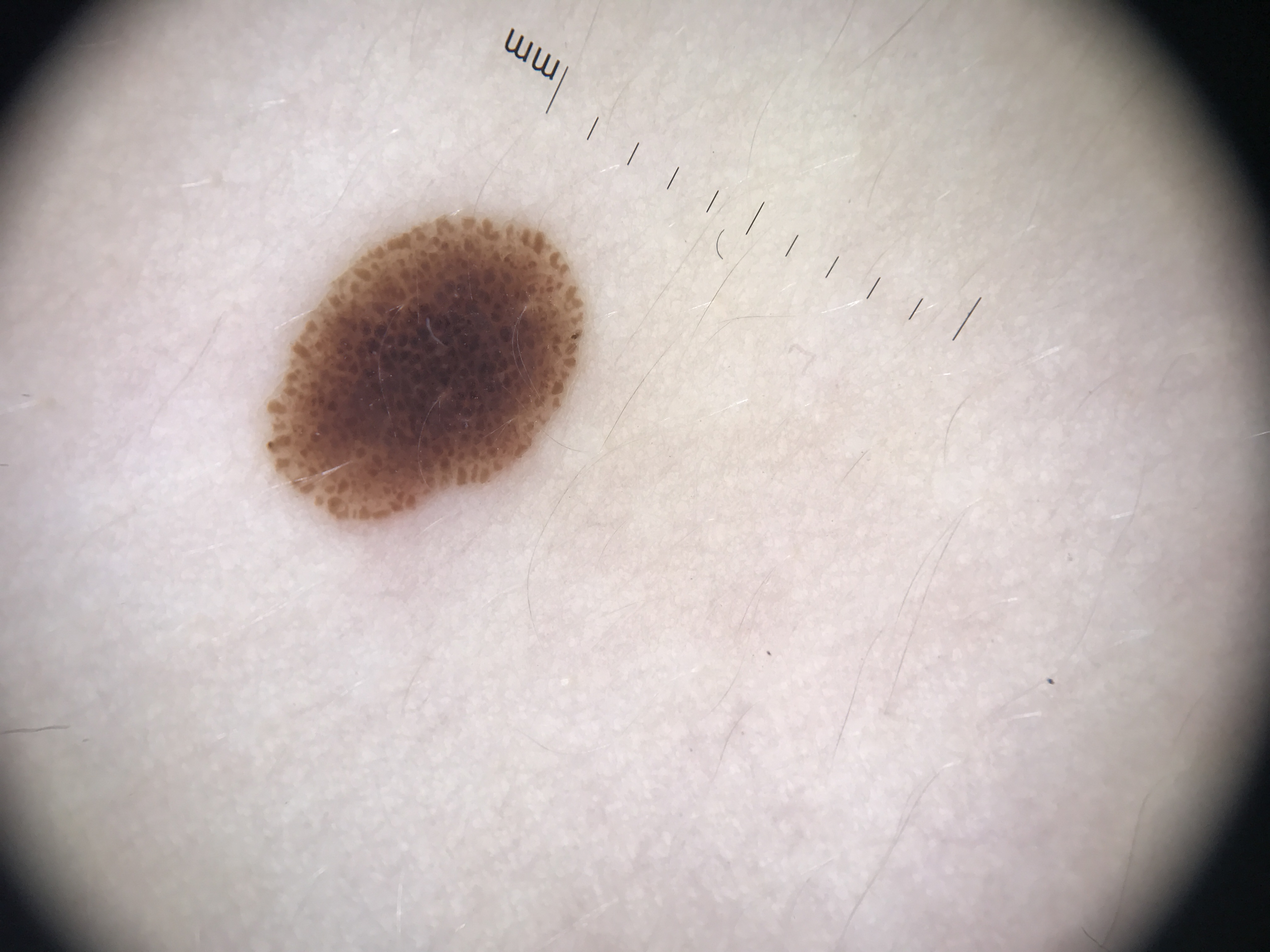assessment — junctional nevus (expert consensus).